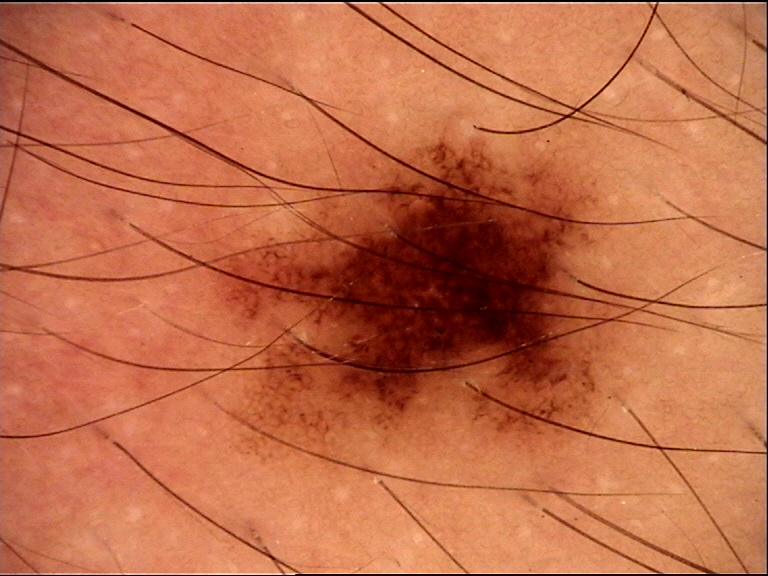A dermoscopic image of a skin lesion. Classified as a dysplastic junctional nevus.